The back of the hand is involved. The photograph was taken at an angle: 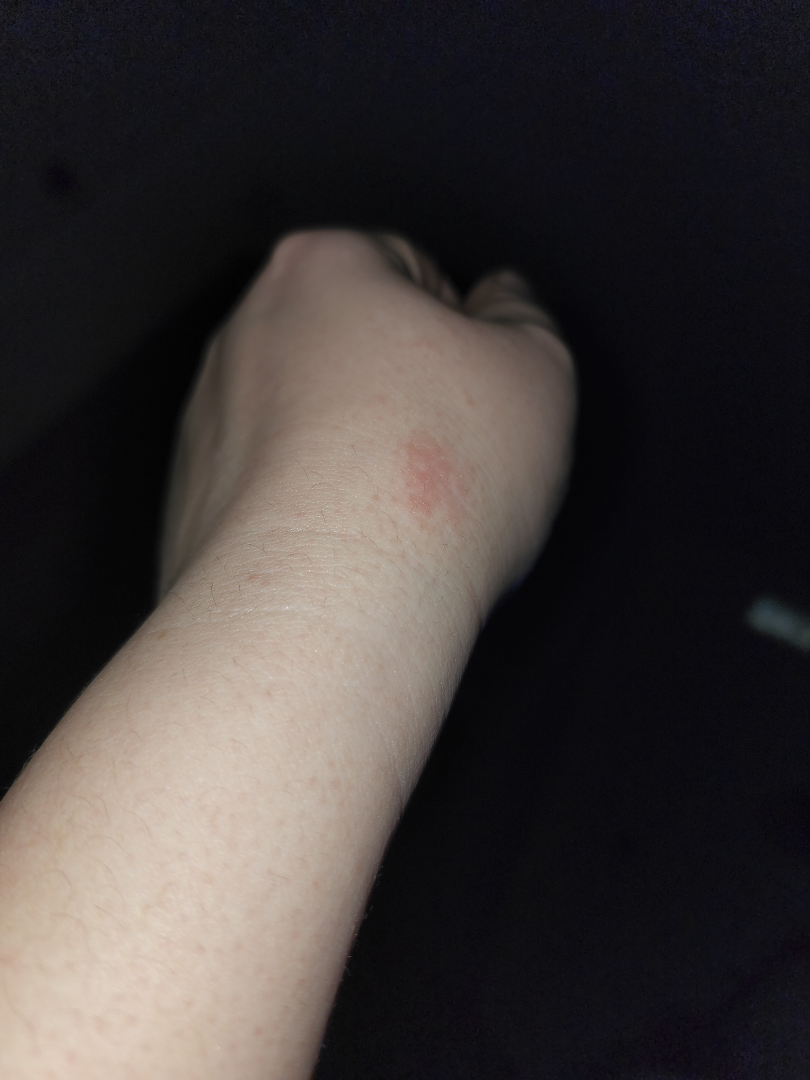constitutional symptoms: none reported, symptoms: itching, lesion texture: raised or bumpy, duration: less than one week, assessment: Eczema (0.50); Allergic Contact Dermatitis (0.50).